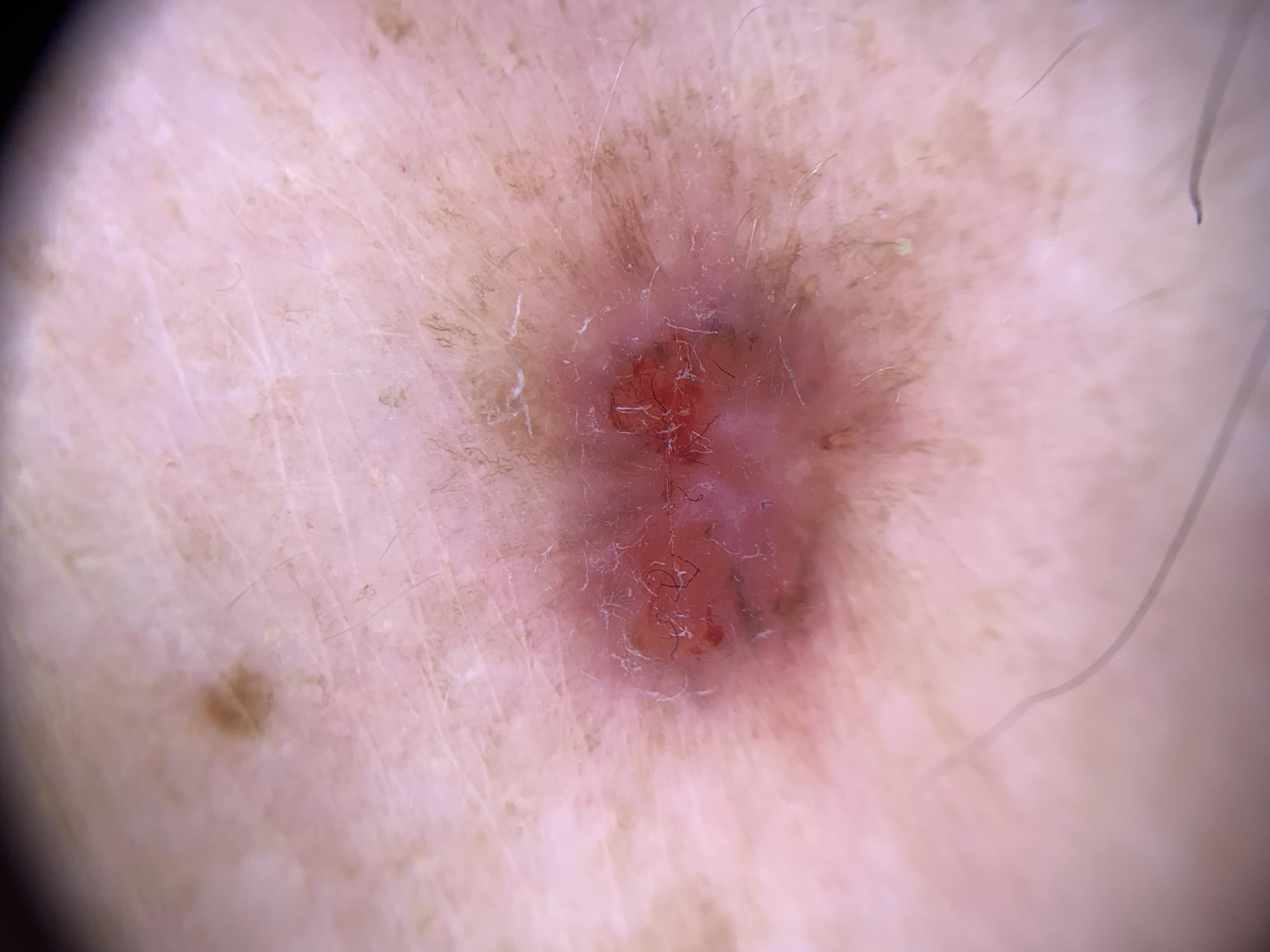Image and clinical context:
A contact-polarized dermoscopy image of a skin lesion. A male patient aged 78-82. Recorded as Fitzpatrick skin type II. Located on the trunk (the anterior trunk).
Conclusion:
Histopathologically confirmed as a tumor of follicular differentiation — a basal cell carcinoma.